A dermoscopic image of a skin lesion. A female subject, roughly 40 years of age:
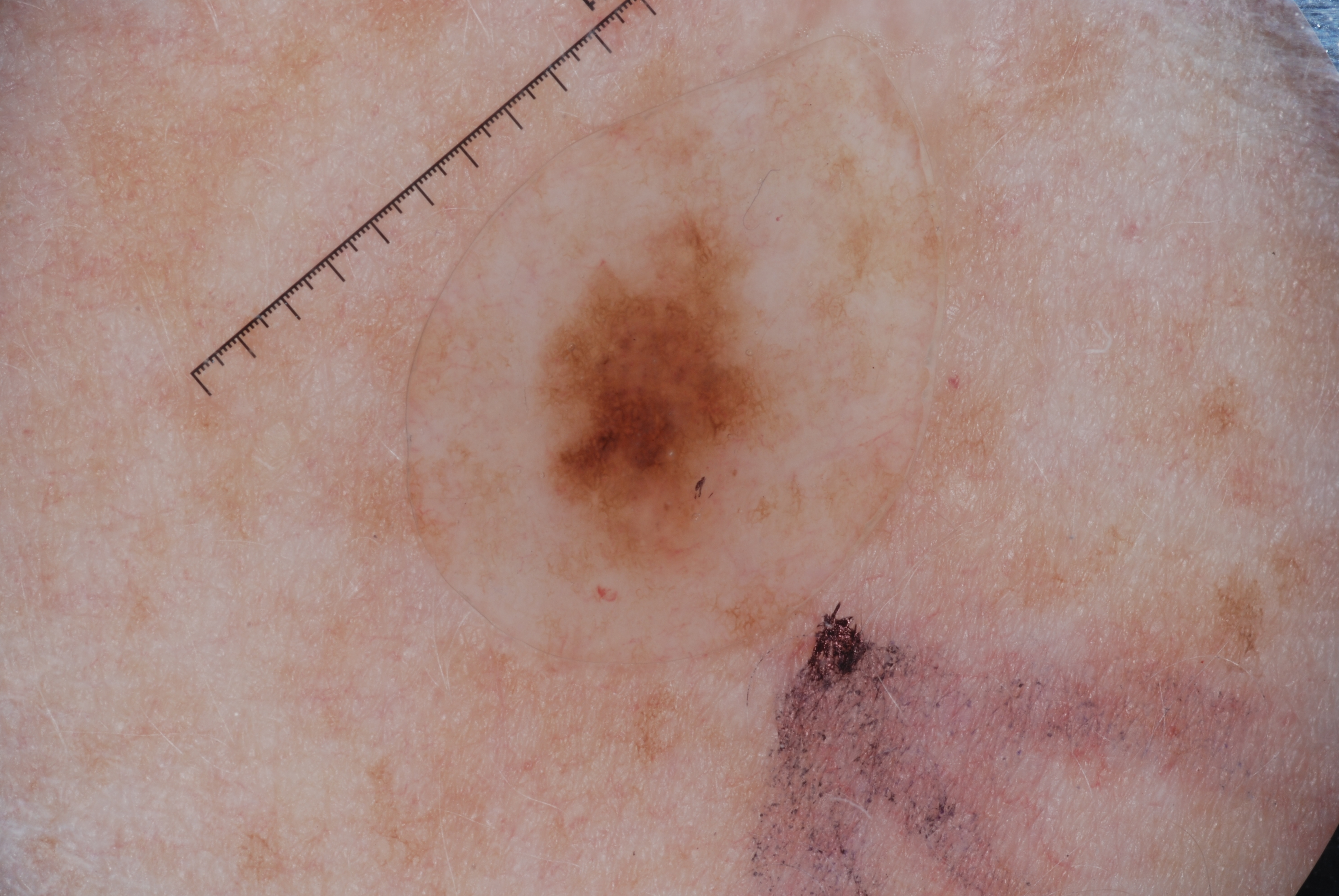location = x1=544 y1=224 x2=784 y2=567, size = small, dermoscopic pattern = pigment network and milia-like cysts; absent: streaks and negative network, impression = a melanocytic nevus.